The palm is involved. Close-up view. Female patient, age 50–59:
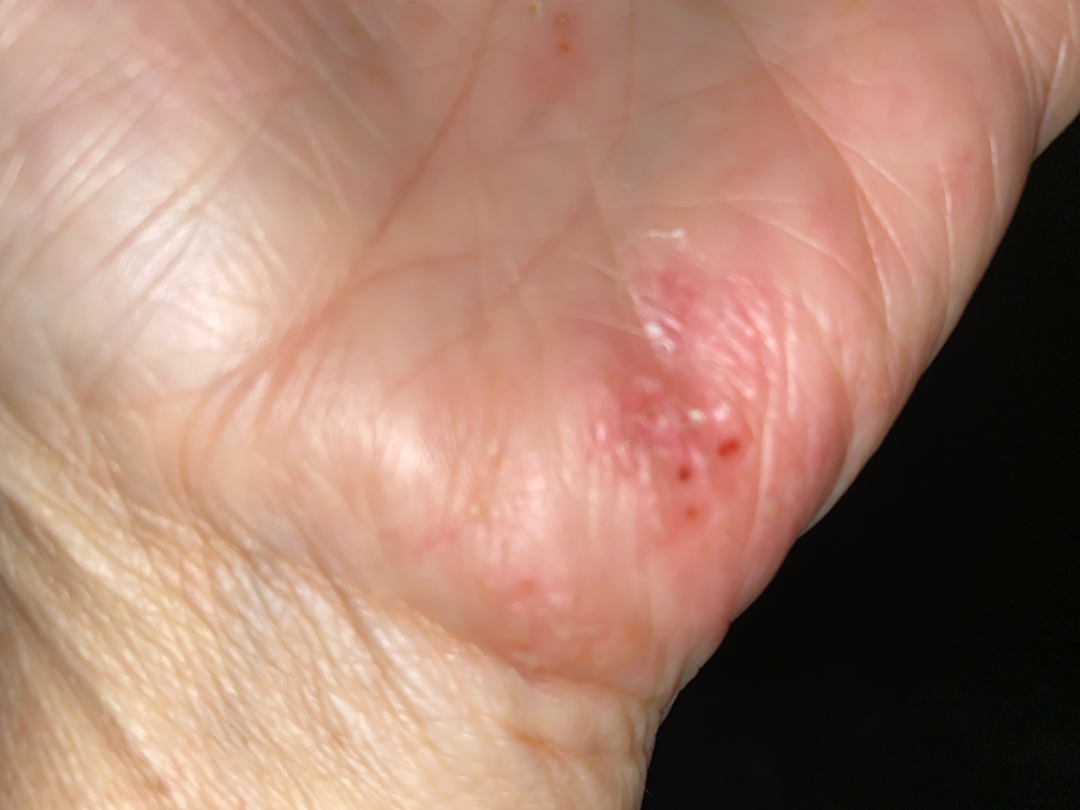The lesion is associated with burning and itching. Texture is reported as raised or bumpy and rough or flaky. The condition has been present for three to twelve months. The patient considered this a rash. The patient notes associated joint pain. Allergic Contact Dermatitis, Eczema and Irritant Contact Dermatitis were considered with similar weight.